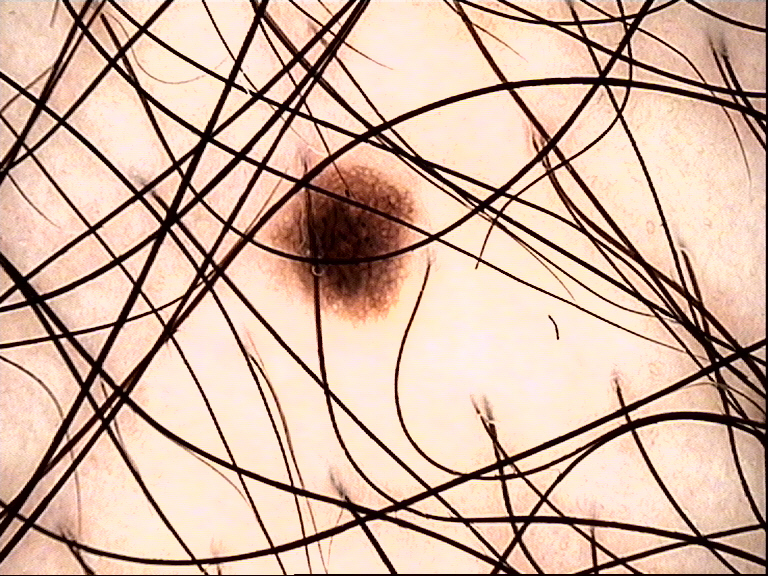Findings:
Dermoscopy of a skin lesion.
Conclusion:
The diagnosis was a benign lesion — a dysplastic junctional nevus.